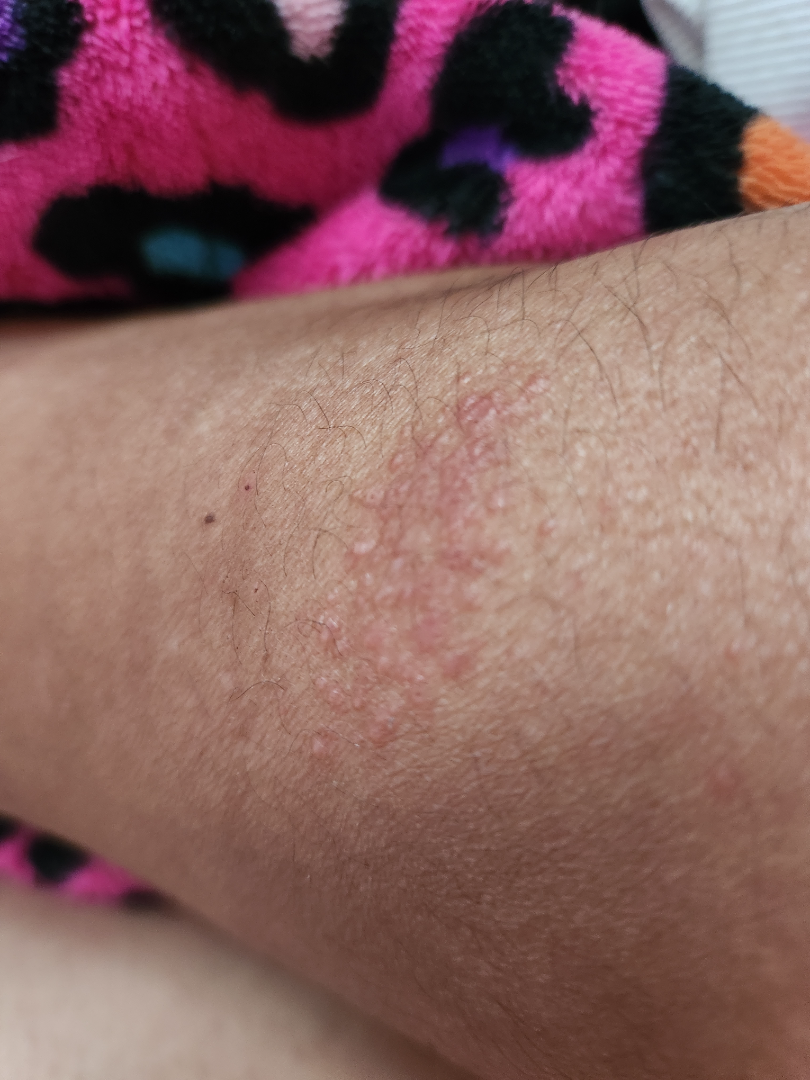The patient notes itching.
A close-up photograph.
Fitzpatrick II.
No relevant systemic symptoms.
Self-categorized by the patient as a rash.
The subject is female.
The arm is involved.
Texture is reported as raised or bumpy.
Eczema (50%); Contact dermatitis (29%); Psoriasis (21%).